A skin lesion imaged with a dermatoscope:
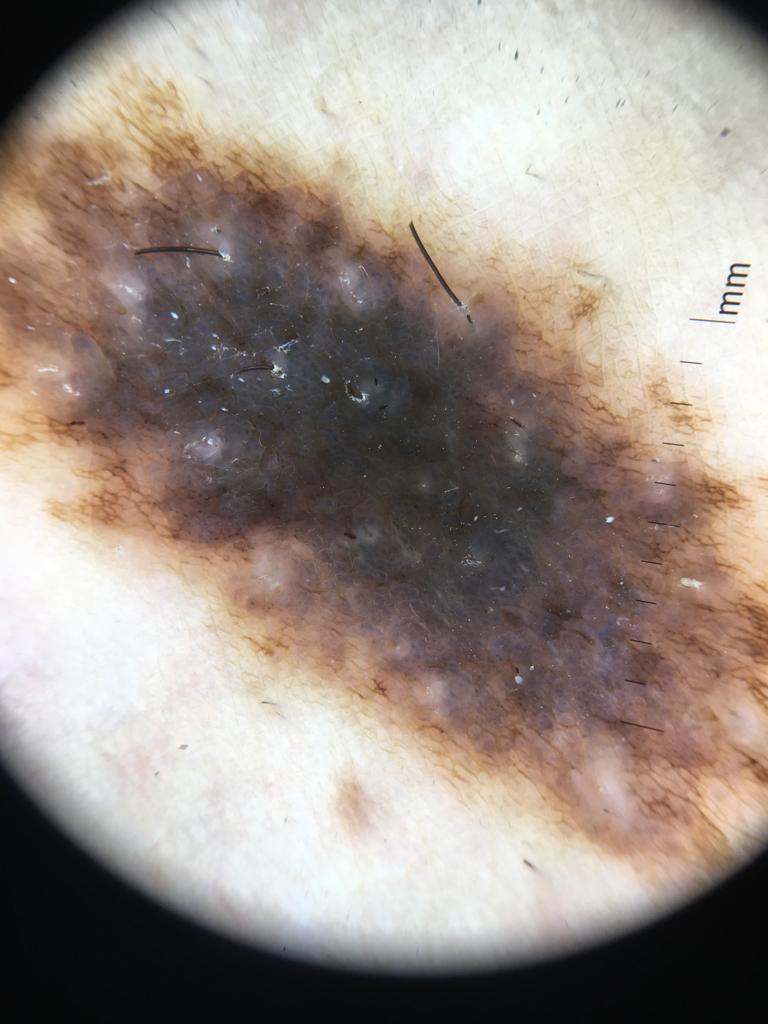Classified as a congenital compound nevus.